The photo was captured at a distance · the condition has been present for one to four weeks · the lesion is described as raised or bumpy · the lesion involves the back of the hand, palm and arm:
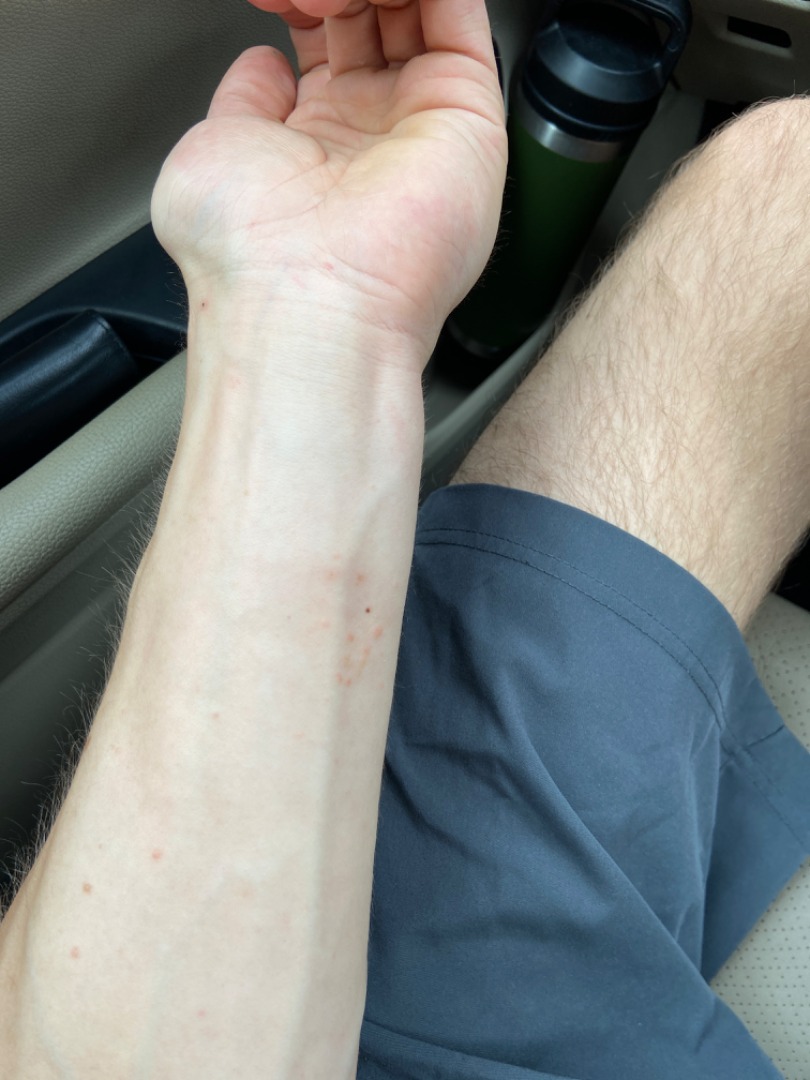  differential:
    tied_lead:
      - Granuloma annulare
      - Insect Bite
      - Allergic Contact Dermatitis